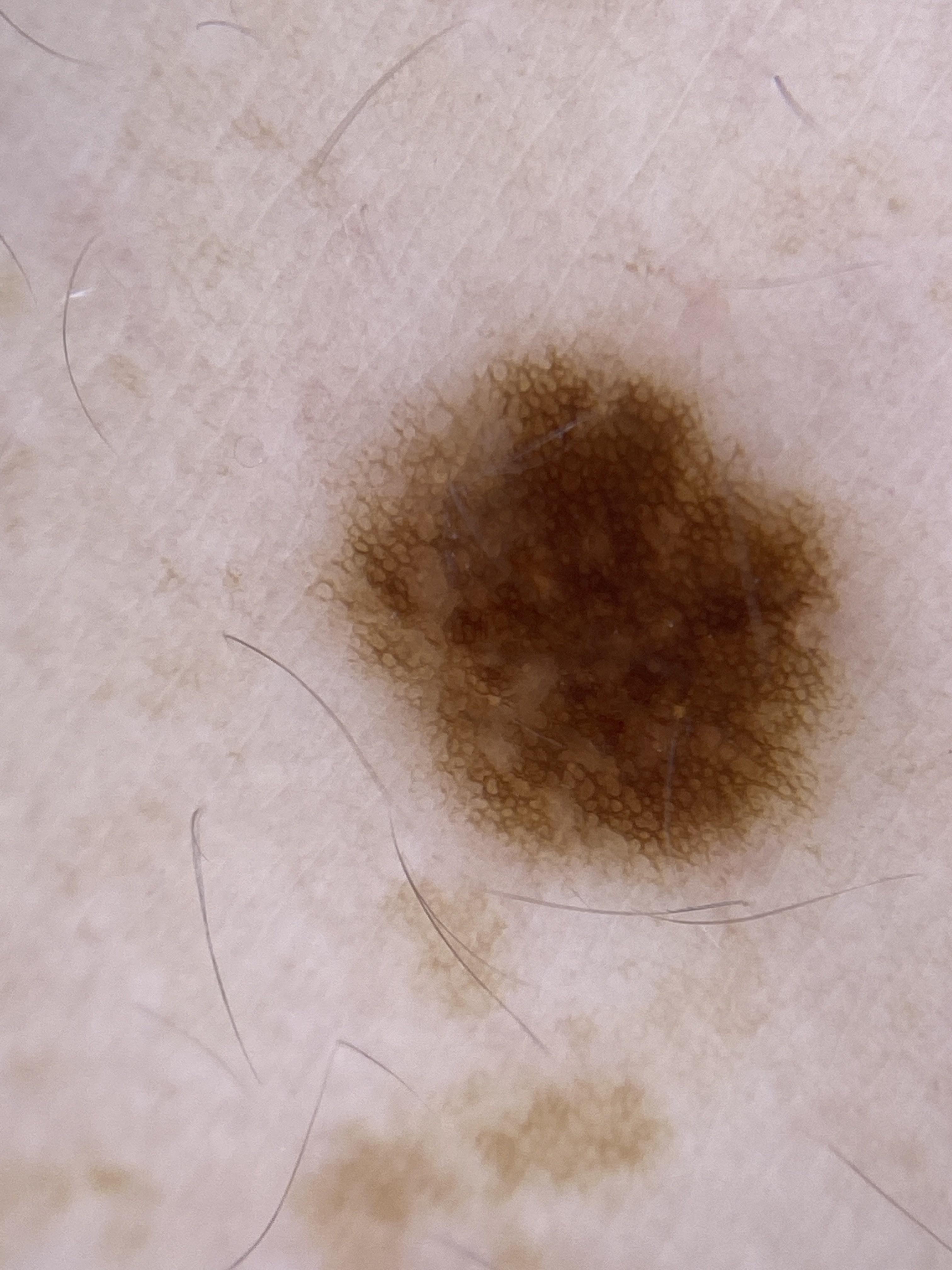modality: dermoscopic image; subject: female, aged 53-57; impression: Nevus.